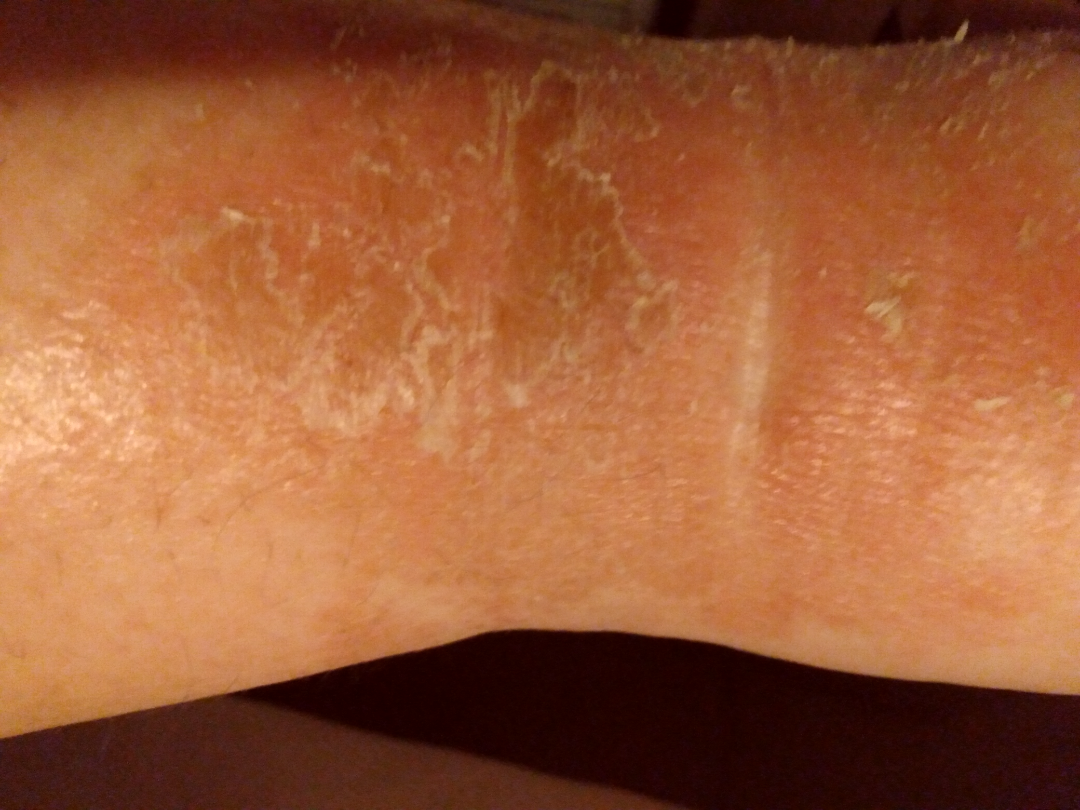Three dermatologists independently reviewed the case: most likely Eczema; a remote consideration is Impetigo; less probable is Stasis Dermatitis; less likely is Ichthyosiform dermatosis.